The chart records prior skin cancer (patient or family), alcohol use, prior malignancy (patient or family), pesticide exposure, and no tobacco use · a clinical close-up photograph of a skin lesion · the patient was assessed as Fitzpatrick III:
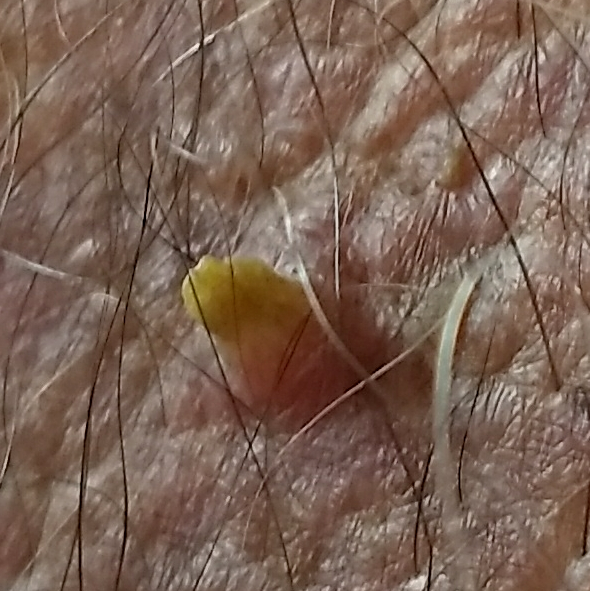Located on the chest. The lesion measures 6 × 5 mm. Histopathological examination showed an actinic keratosis.